A close-up photograph · the affected area is the leg:
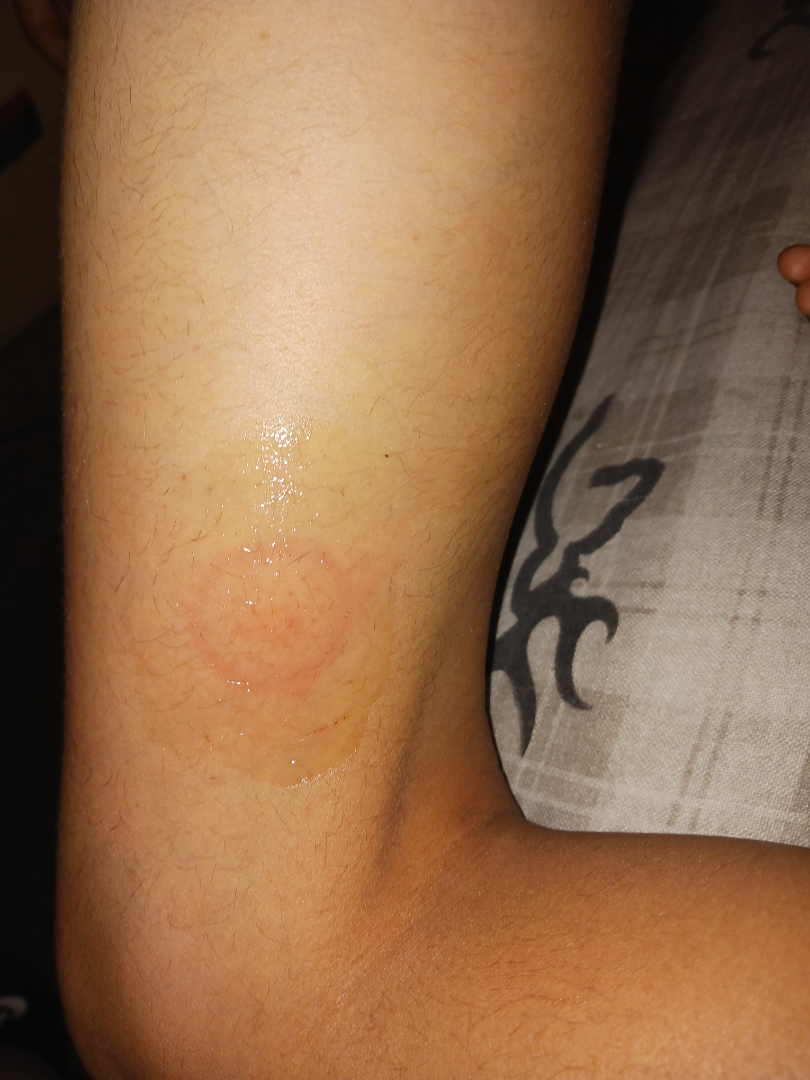{"differential": {"tied_lead": ["Allergic Contact Dermatitis", "Irritant Contact Dermatitis"]}}